This is a dermoscopic photograph of a skin lesion; the subject is a male aged around 40:
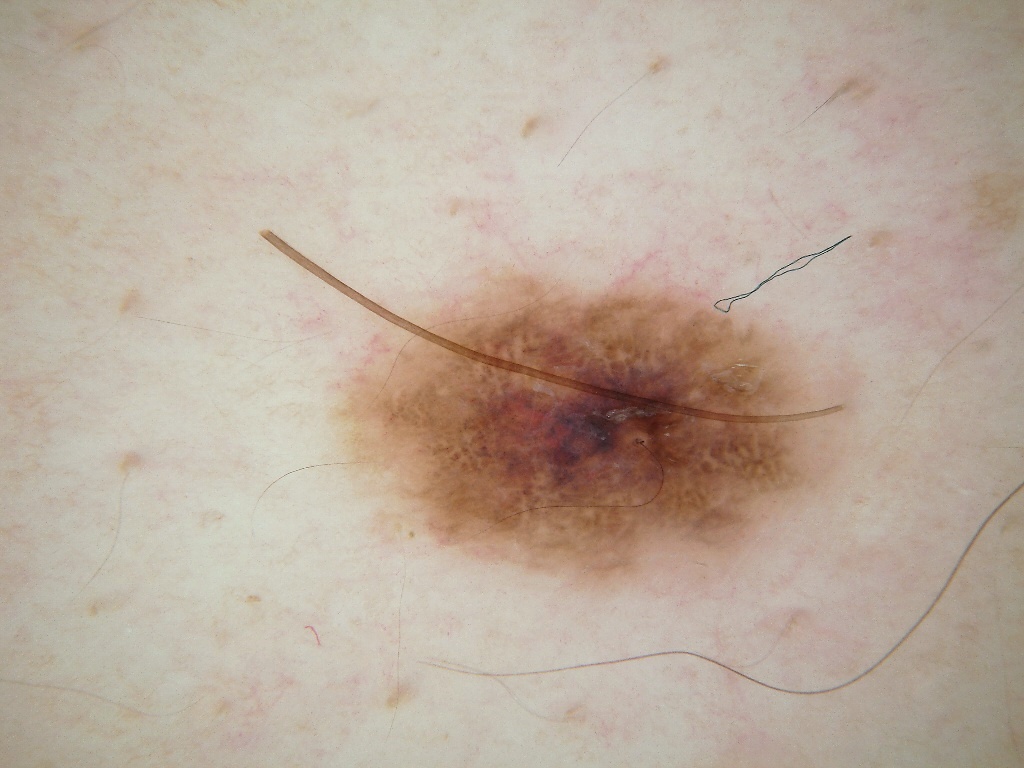Image and clinical context:
The lesion occupies the region <box>314, 248, 838, 606</box>. A mid-sized lesion within the field. Dermoscopic assessment notes globules and negative network.
Pathology:
The biopsy diagnosis was a melanoma.